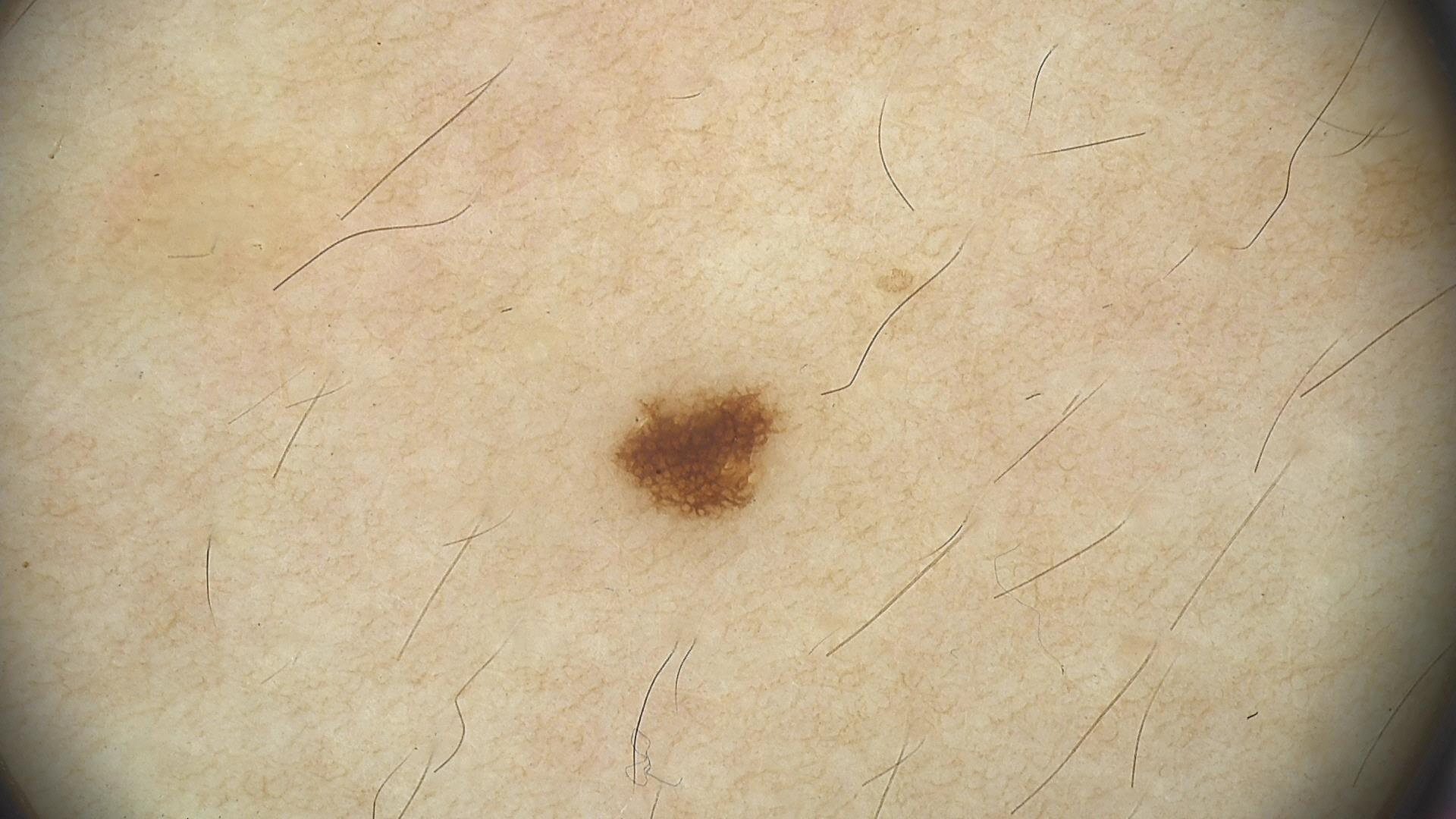Q: What is the diagnosis?
A: junctional nevus (expert consensus)